Close-up view · the contributor is 50–59, female · the lesion involves the leg — 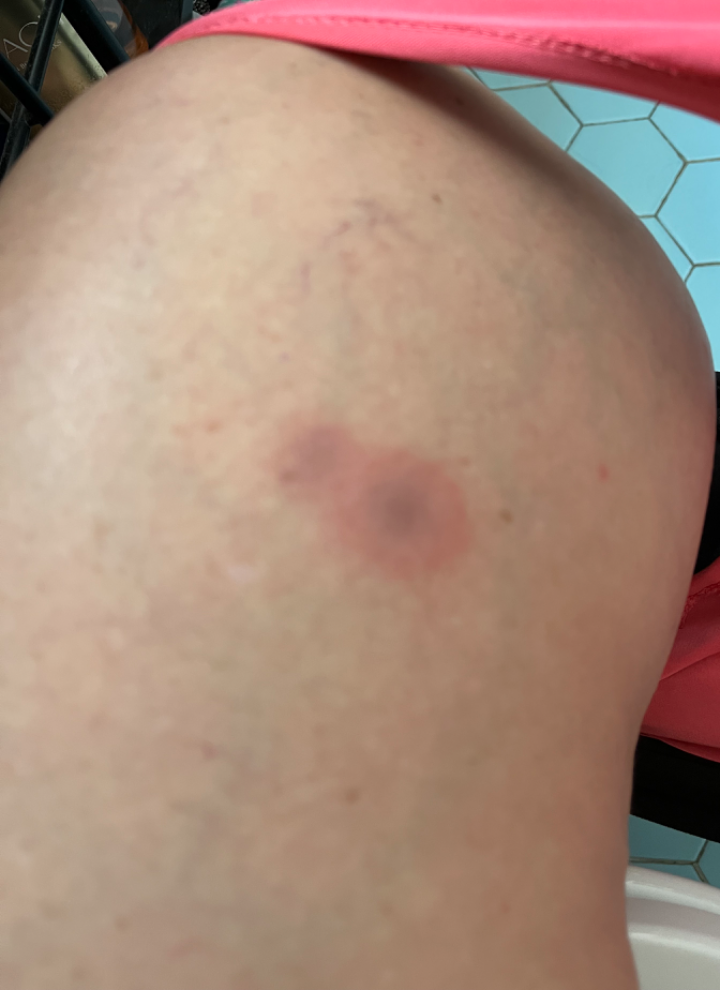Reviewed remotely by one dermatologist: most likely Geographic tongue; the differential also includes Insect Bite; less probable is Erythema multiforme.